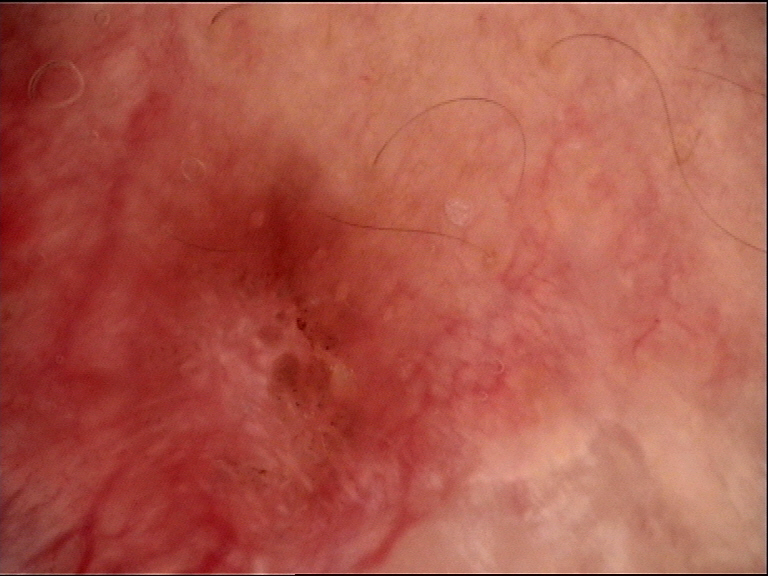Findings:
• diagnostic label · basal cell carcinoma (biopsy-proven)